A dermoscopy image of a single skin lesion: 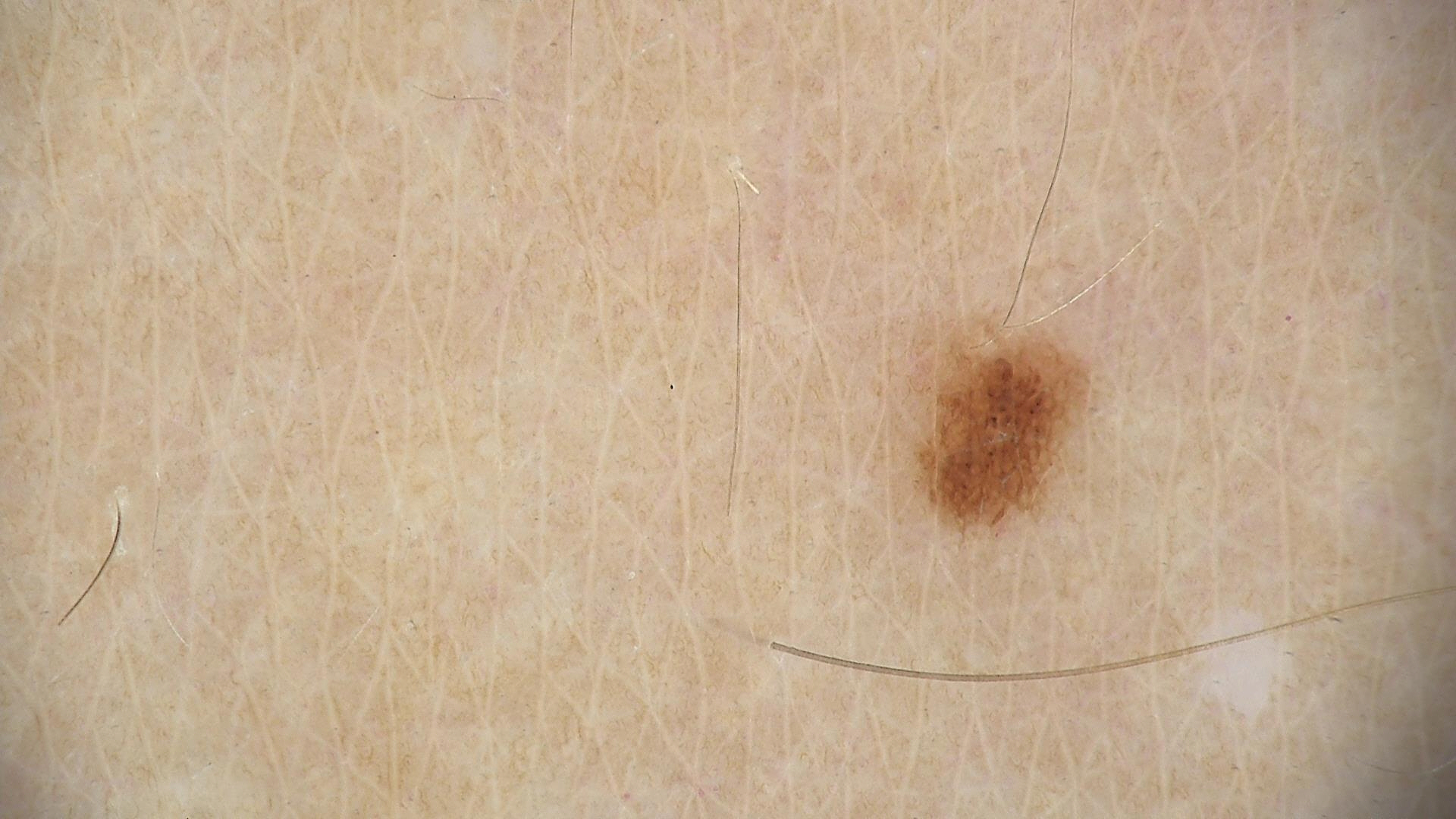Labeled as a dysplastic junctional nevus.